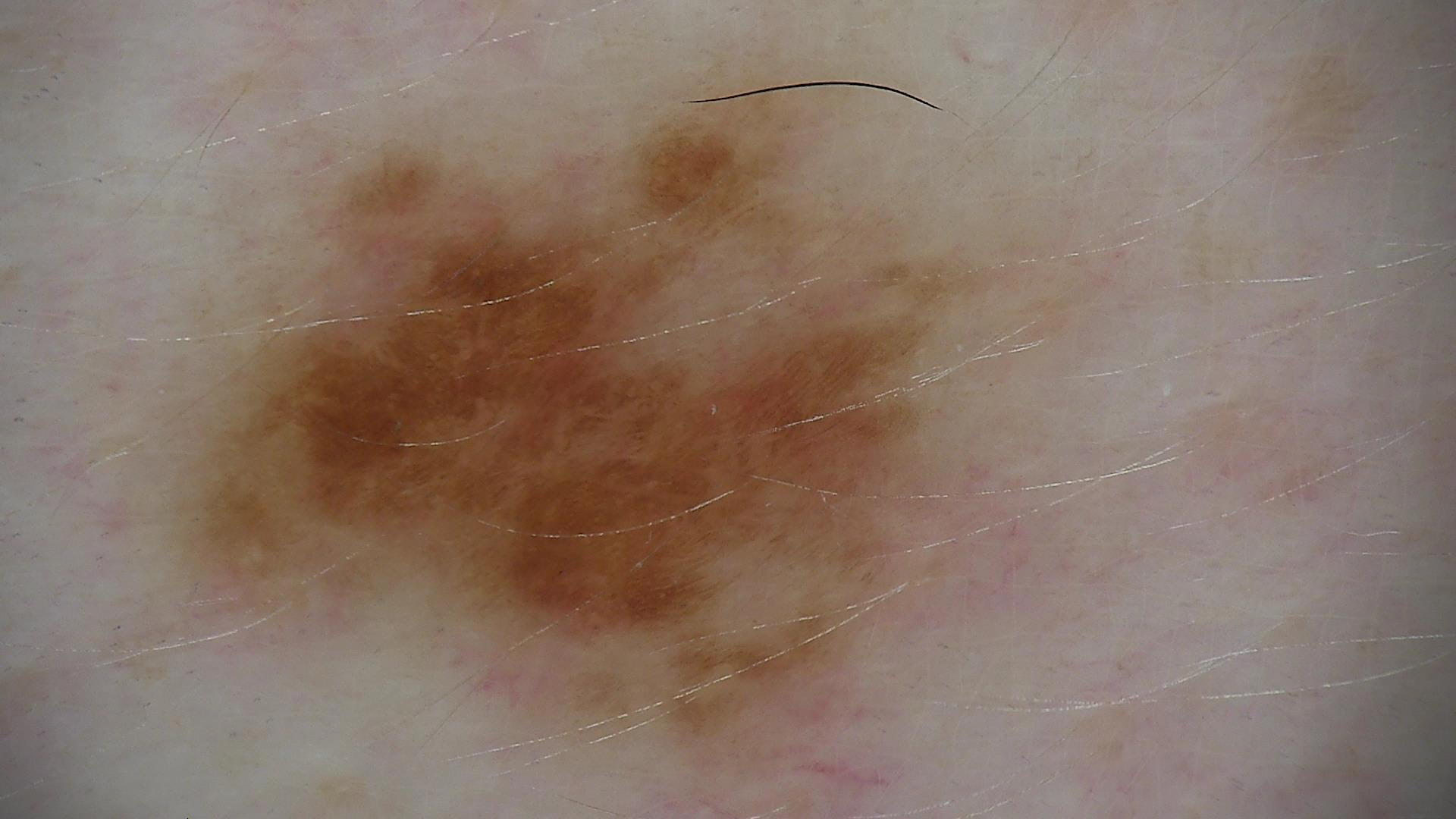The diagnosis was a dysplastic junctional nevus.